A skin lesion imaged with a dermatoscope · the subject is a female approximately 45 years of age — 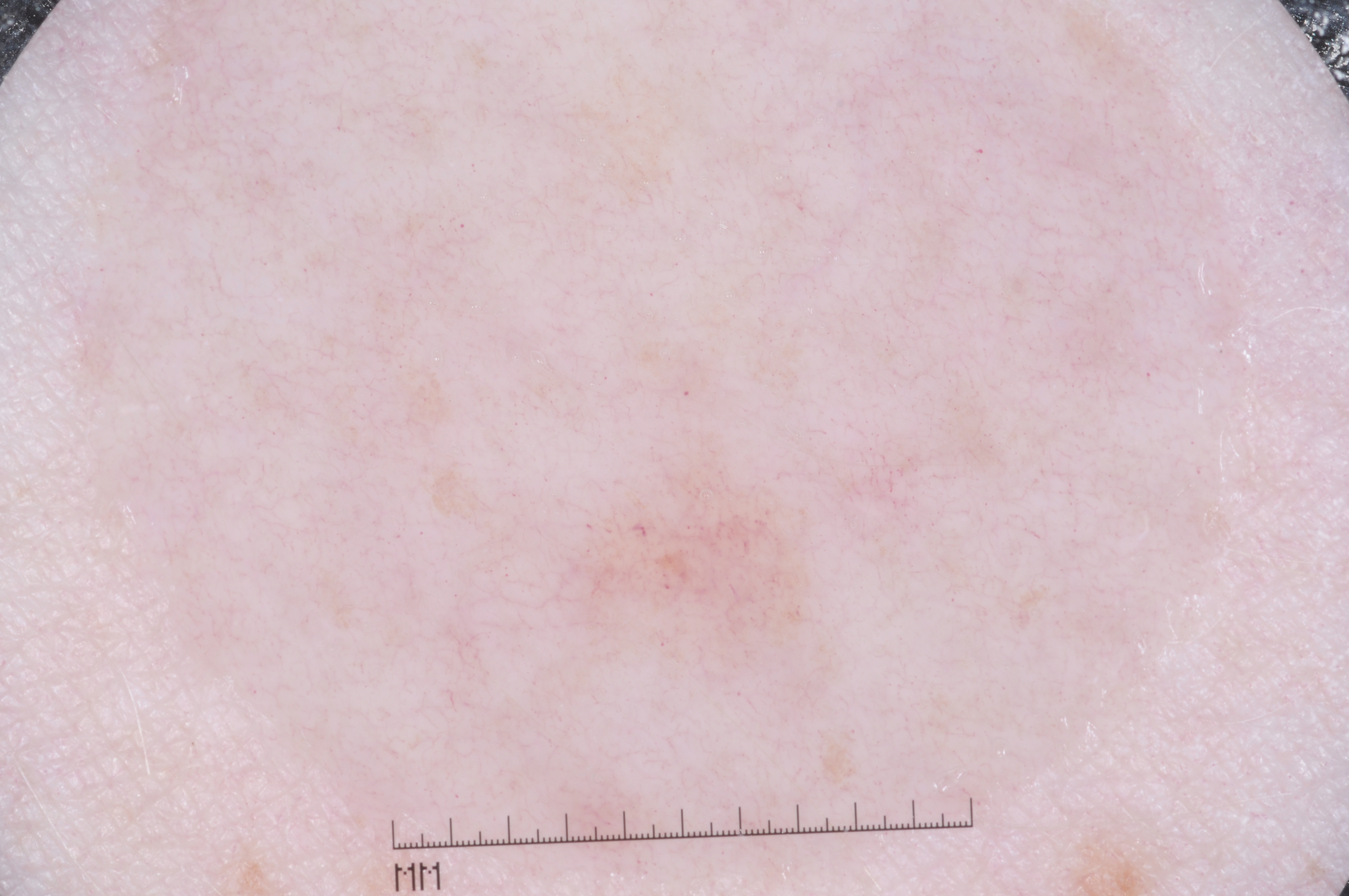- size · small
- absent dermoscopic features · streaks, pigment network, milia-like cysts, and negative network
- bounding box · bbox(580, 462, 811, 651)
- diagnosis · a melanocytic nevus, a benign lesion